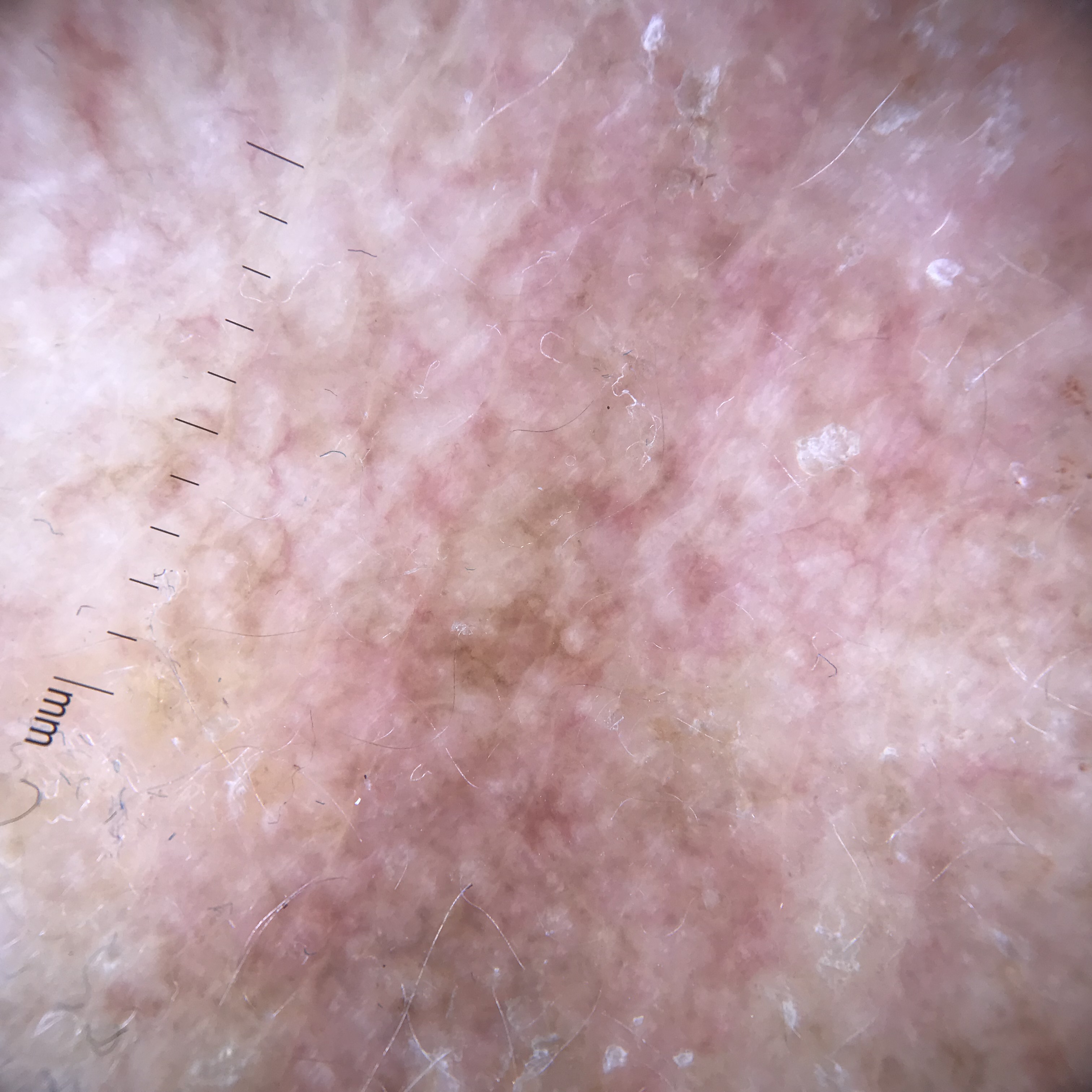Q: How is the lesion classified?
A: keratinocytic
Q: What is this lesion?
A: actinic keratosis (expert consensus)